Located on the back of the hand, leg and arm. The contributor is a female aged 18–29. This image was taken at an angle.
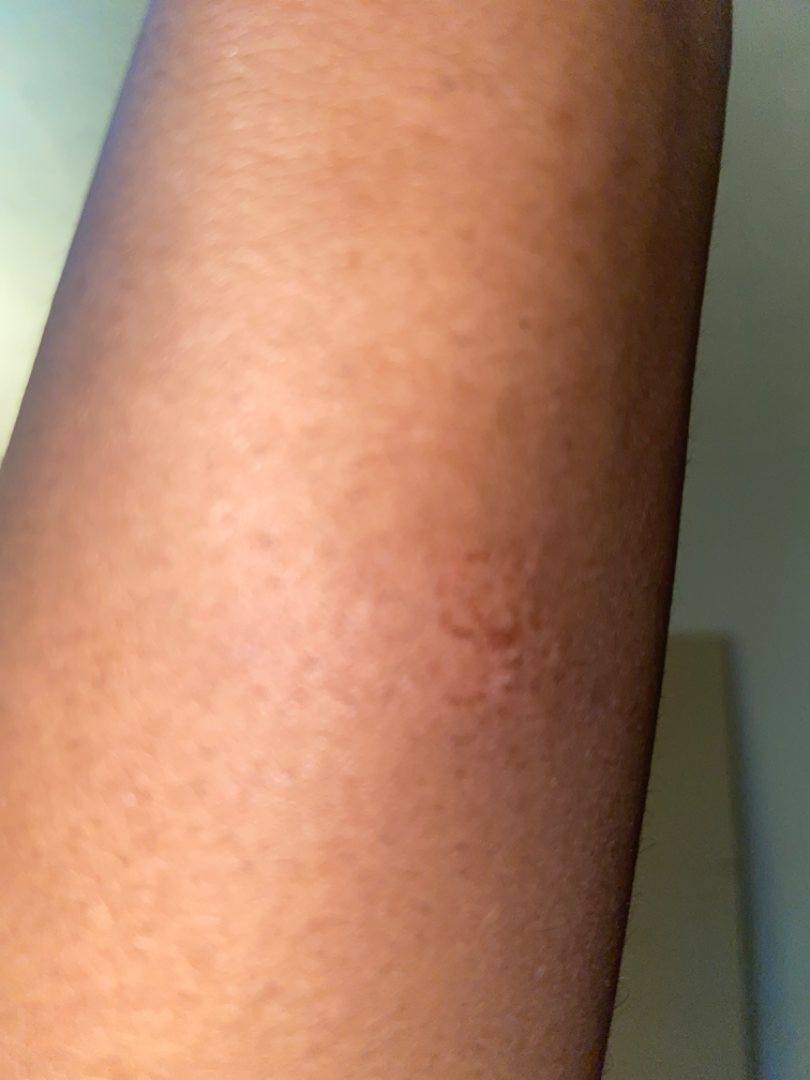dermatologist impression: the differential, in no particular order, includes Abscess, Impetigo and Insect Bite.